A female patient aged 91. A clinical photograph showing a skin lesion.
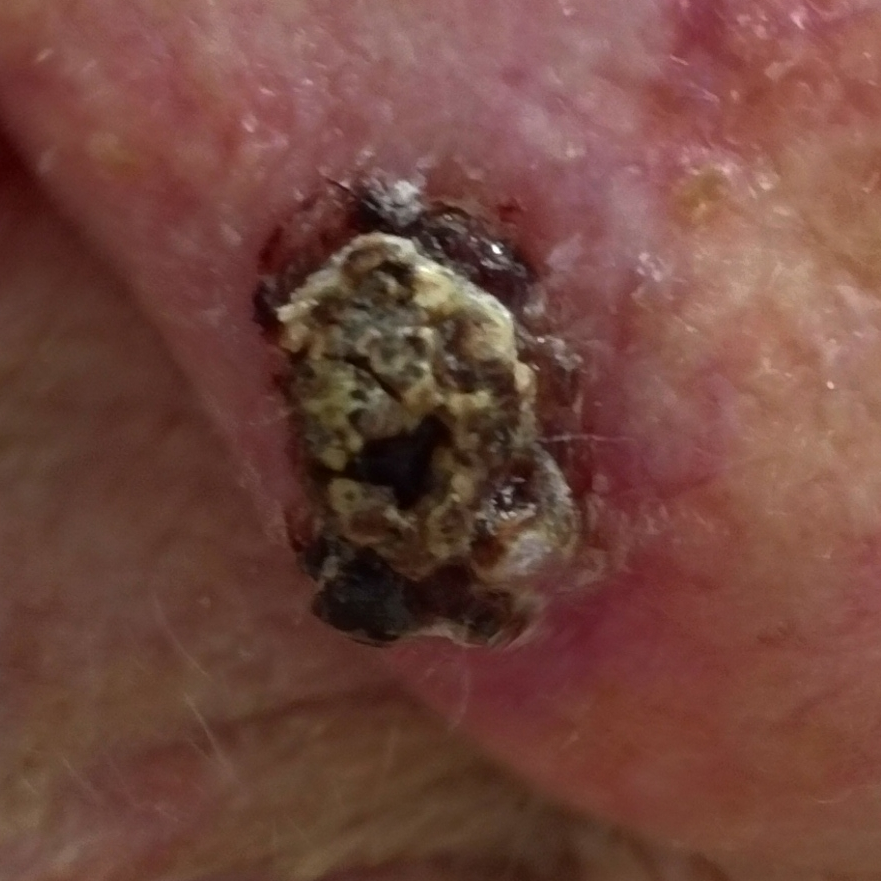  diagnosis:
    name: basal cell carcinoma
    code: BCC
    malignancy: malignant
    confirmation: histopathology